A female patient age 68. A dermatoscopic image of a skin lesion. Imaged for a research study, with no referral diagnosis recorded.
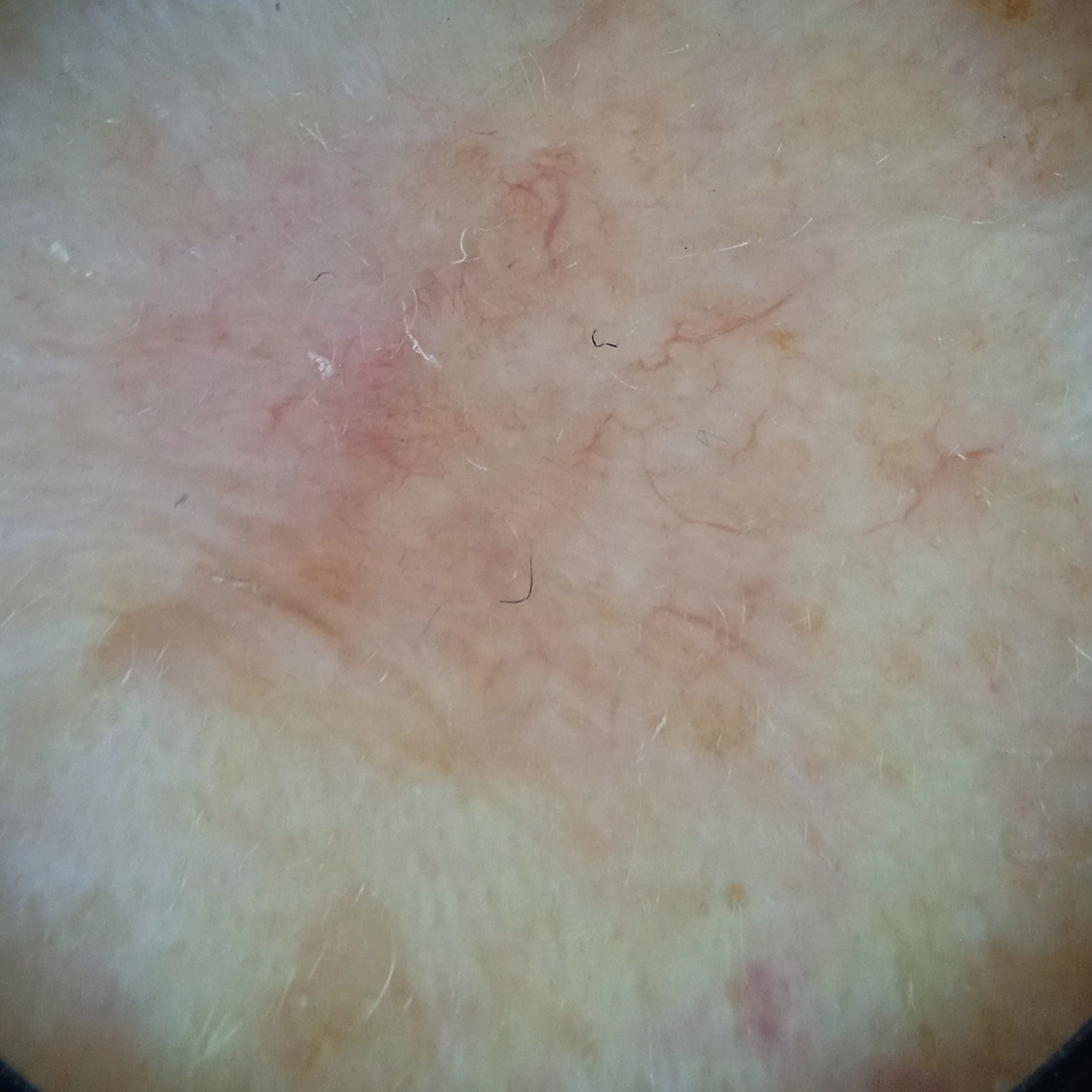{"lesion_location": "the face", "lesion_size": {"diameter_mm": 8.2}, "diagnosis": {"name": "basal cell carcinoma", "malignancy": "malignant", "unanimous": false}}